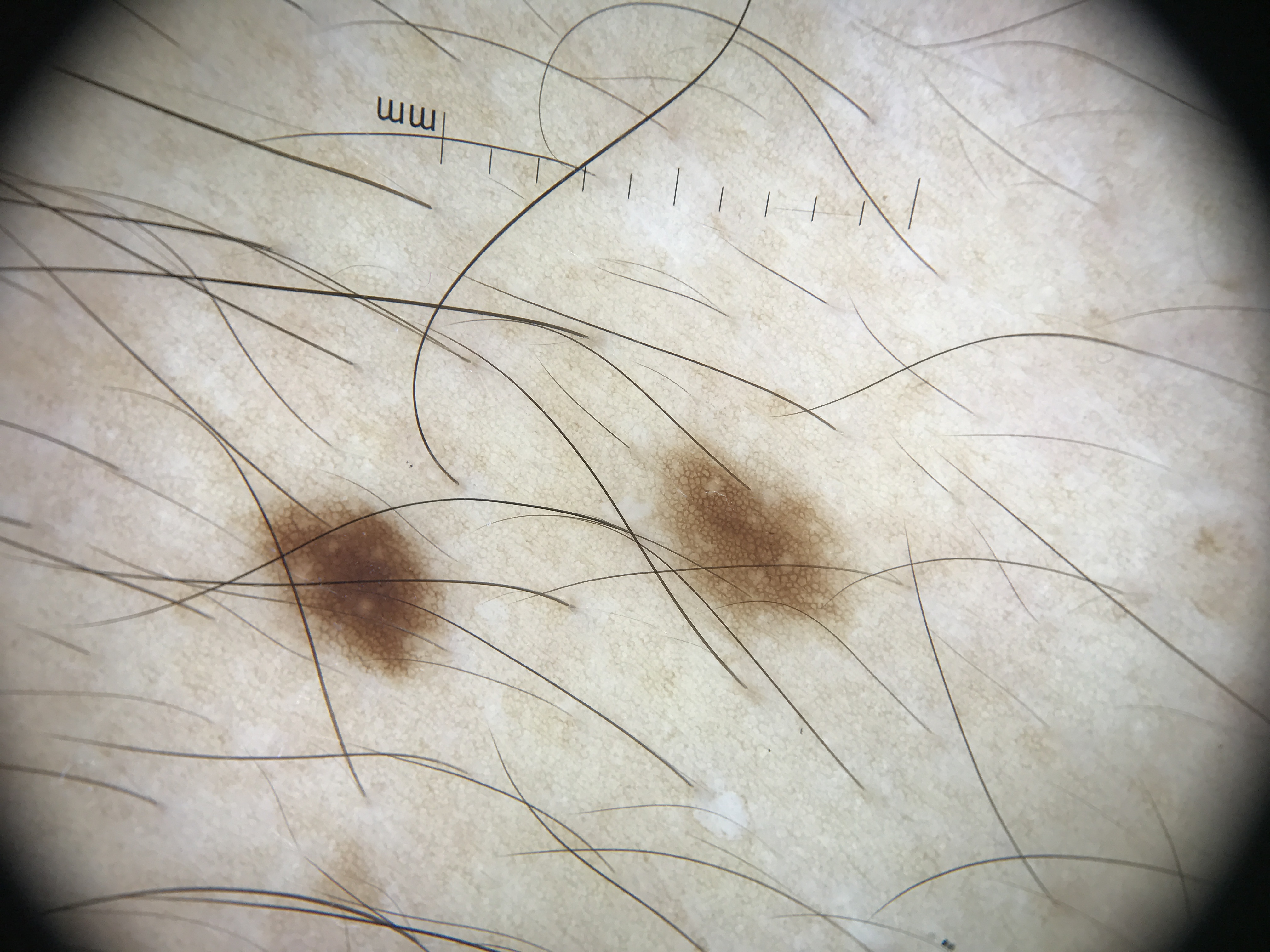Summary: Dermoscopy of a skin lesion. The architecture is that of a banal lesion. Impression: Consistent with a junctional nevus.